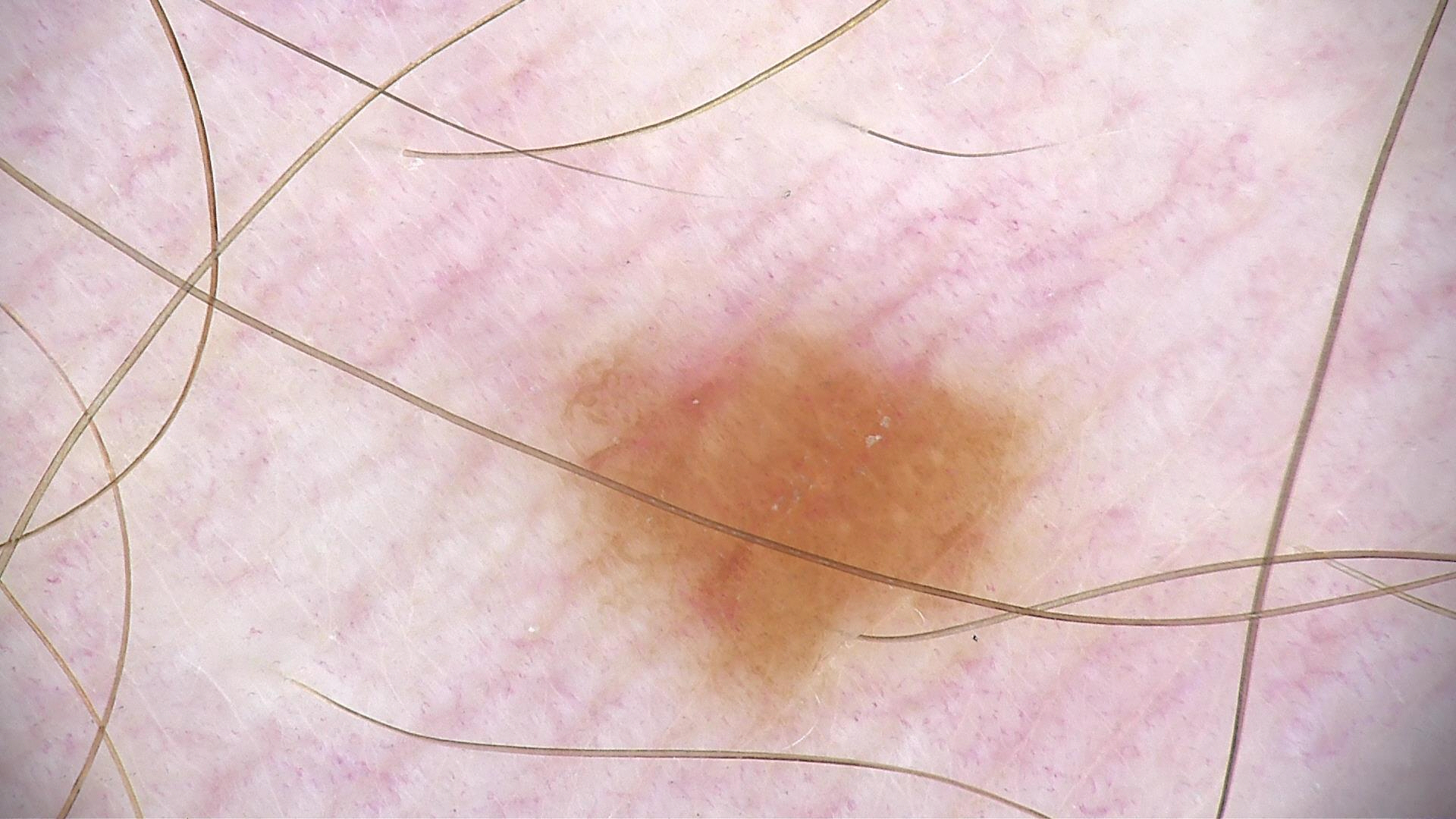Q: What was the diagnostic impression?
A: dysplastic junctional nevus (expert consensus)